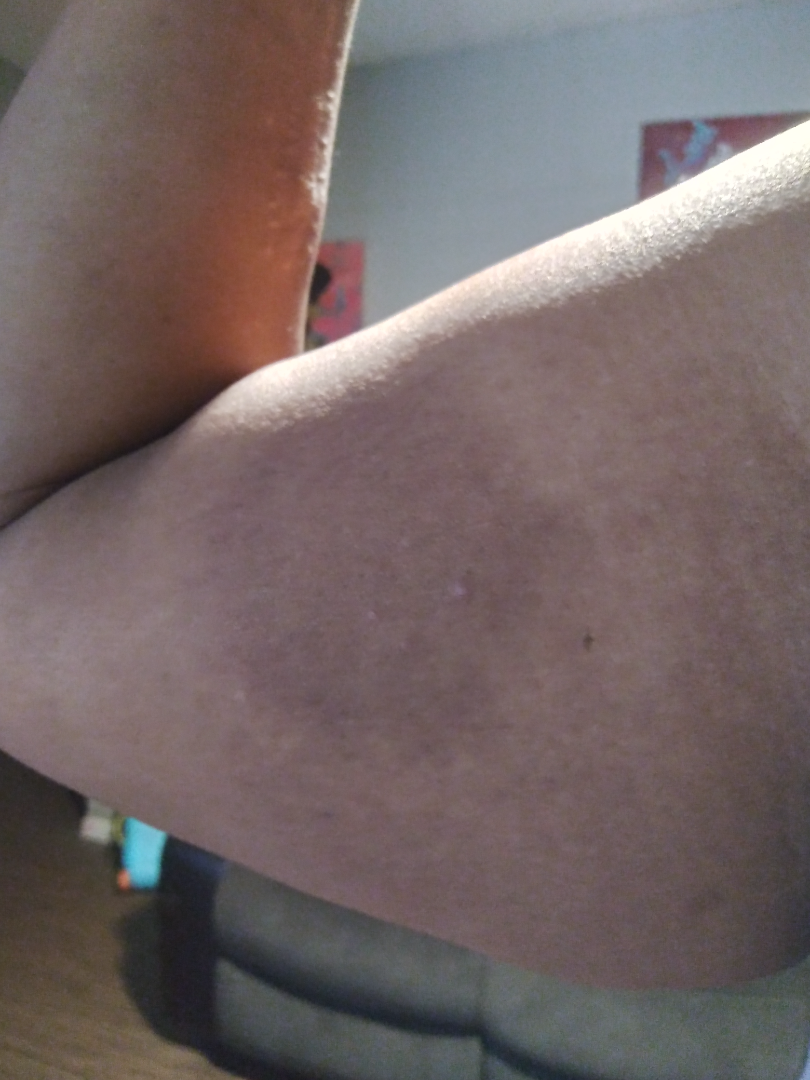– assessment — ungradable on photographic review
– described texture — rough or flaky
– location — arm
– shot type — close-up
– self-categorized as — skin that appeared healthy to them
– skin tone — human graders estimated Monk Skin Tone 4–5